The contributor notes the lesion is flat · the condition has been present for less than one week · the patient described the issue as skin that appeared healthy to them · the lesion involves the leg · this image was taken at an angle: 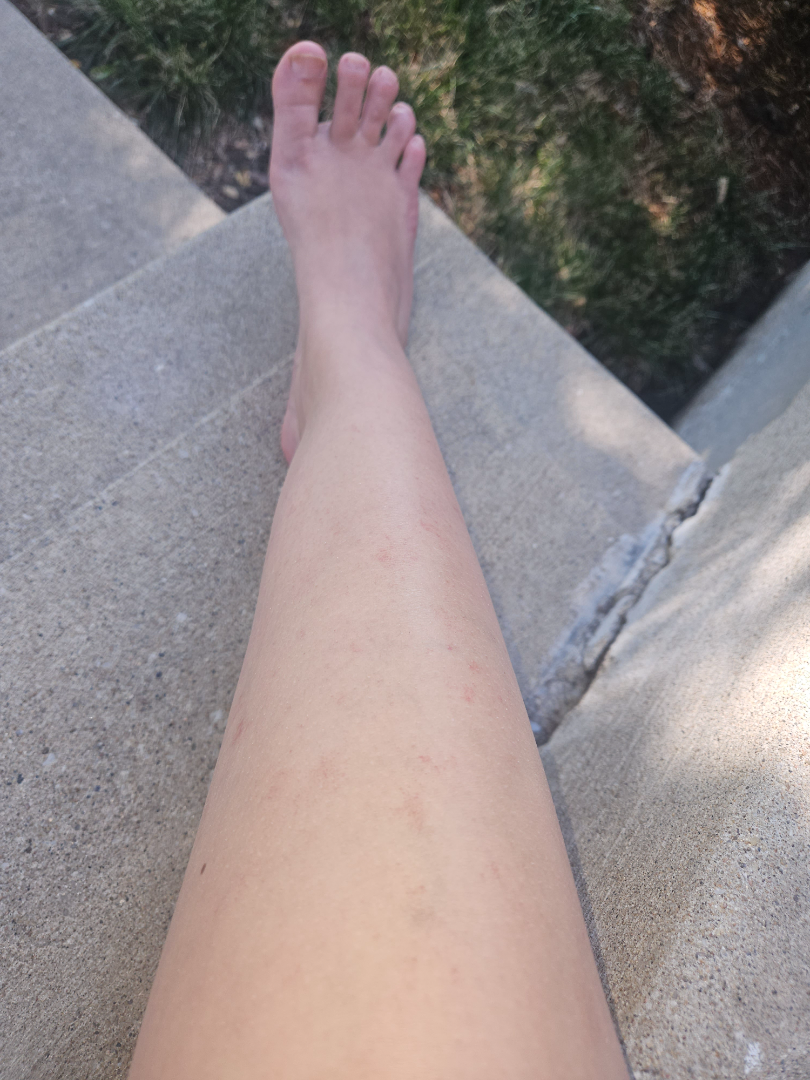Case summary:
* assessment · could not be assessed